A dermatoscopic image of a skin lesion.
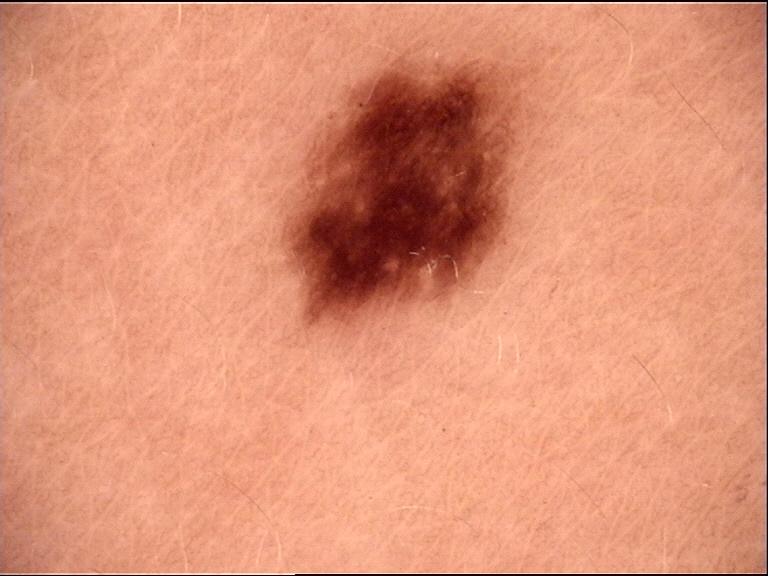Conclusion: The diagnosis was a dysplastic junctional nevus.